A male subject, in their mid- to late 50s. Dermoscopy of a skin lesion:
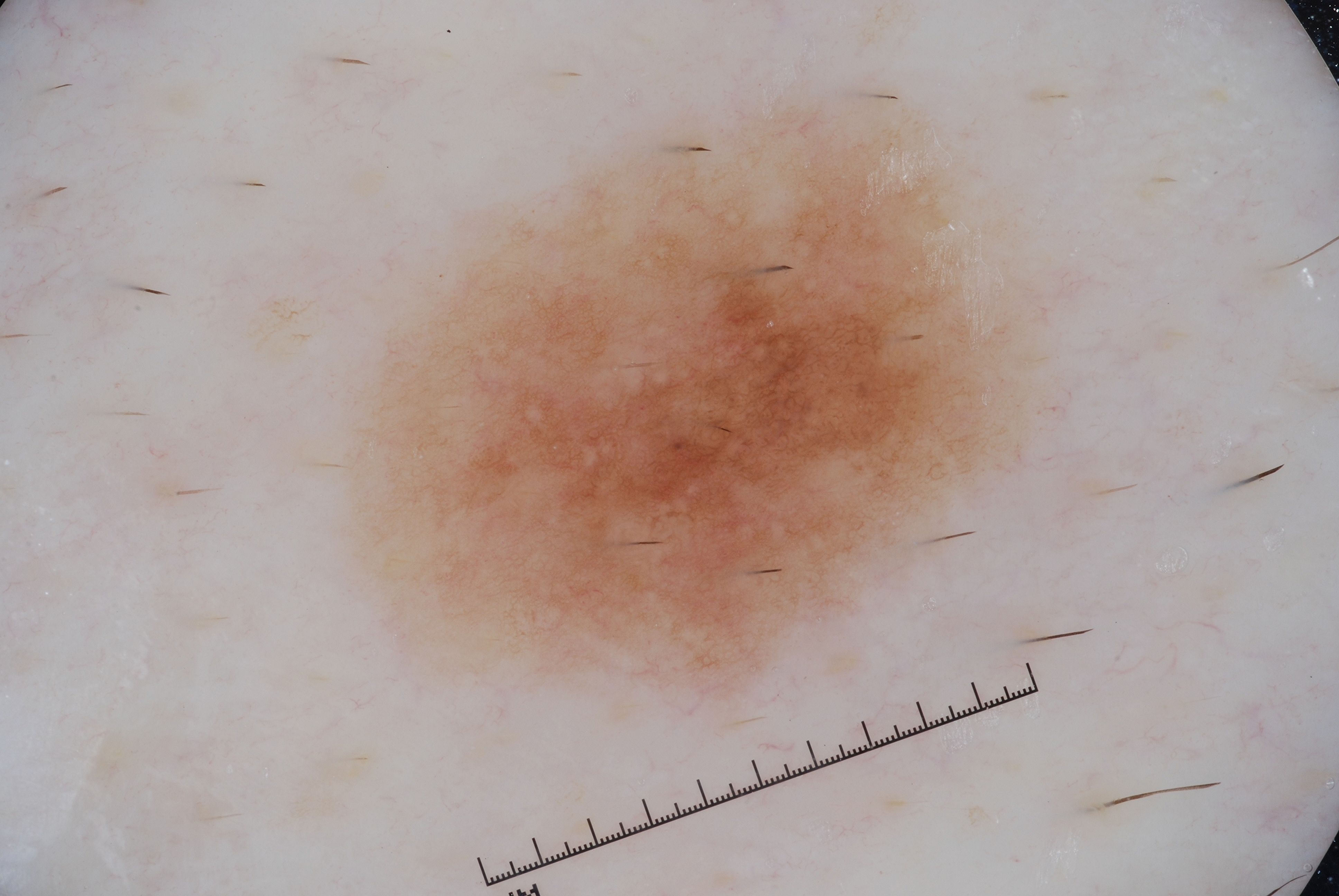dermoscopic features — pigment network and milia-like cysts; absent: streaks and negative network | lesion bbox — 356/98/1025/693 | diagnostic label — a melanoma.